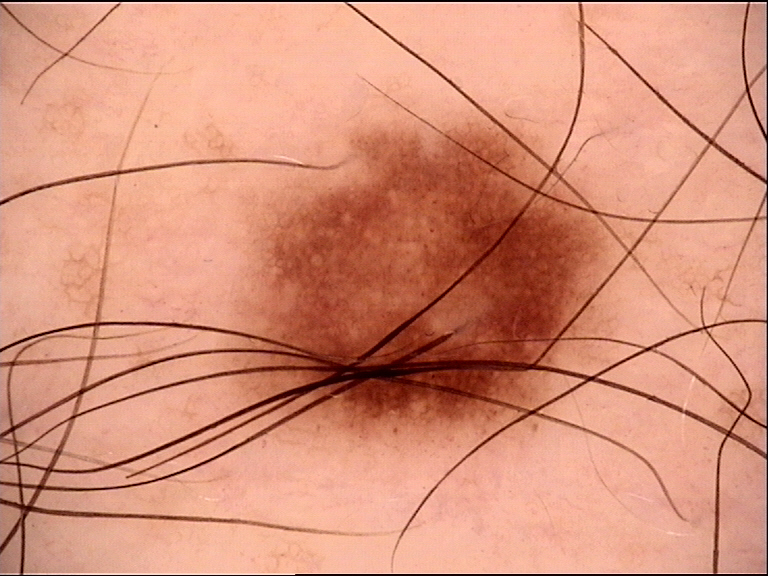- class · dysplastic junctional nevus (expert consensus)